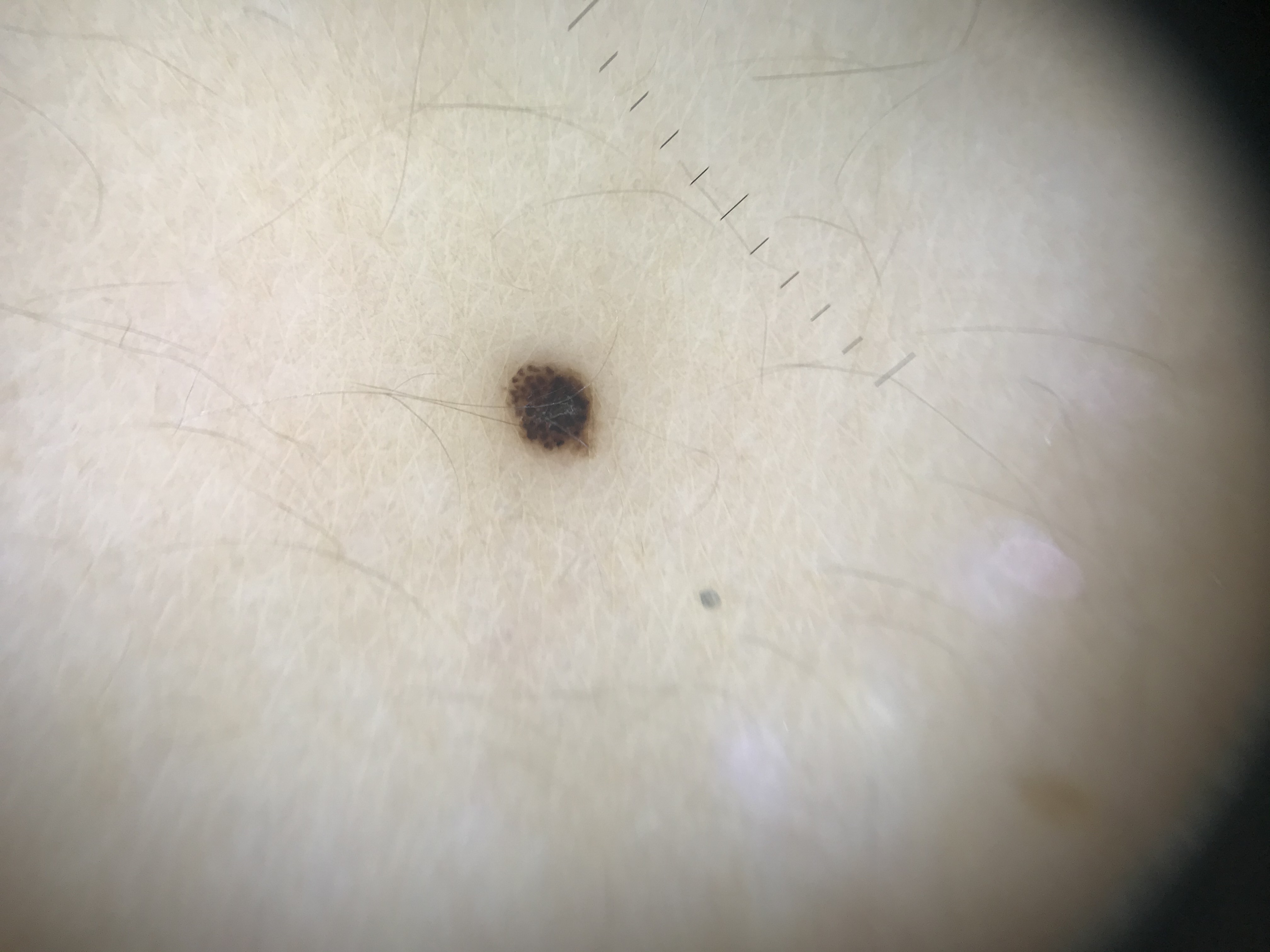Conclusion: The diagnostic label was a junctional nevus.